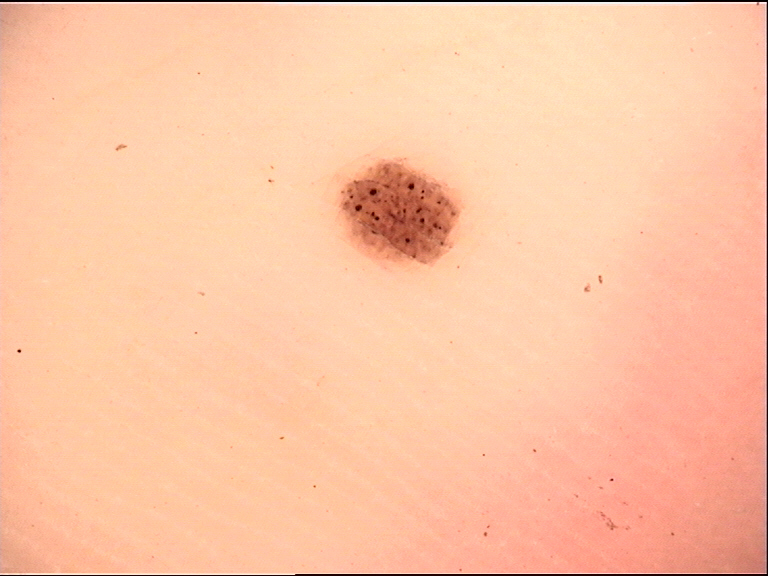A dermoscopic image of a skin lesion. Consistent with an acral dysplastic junctional nevus.